The photo was captured at an angle, the arm and head or neck are involved, the patient is a female aged 30–39:
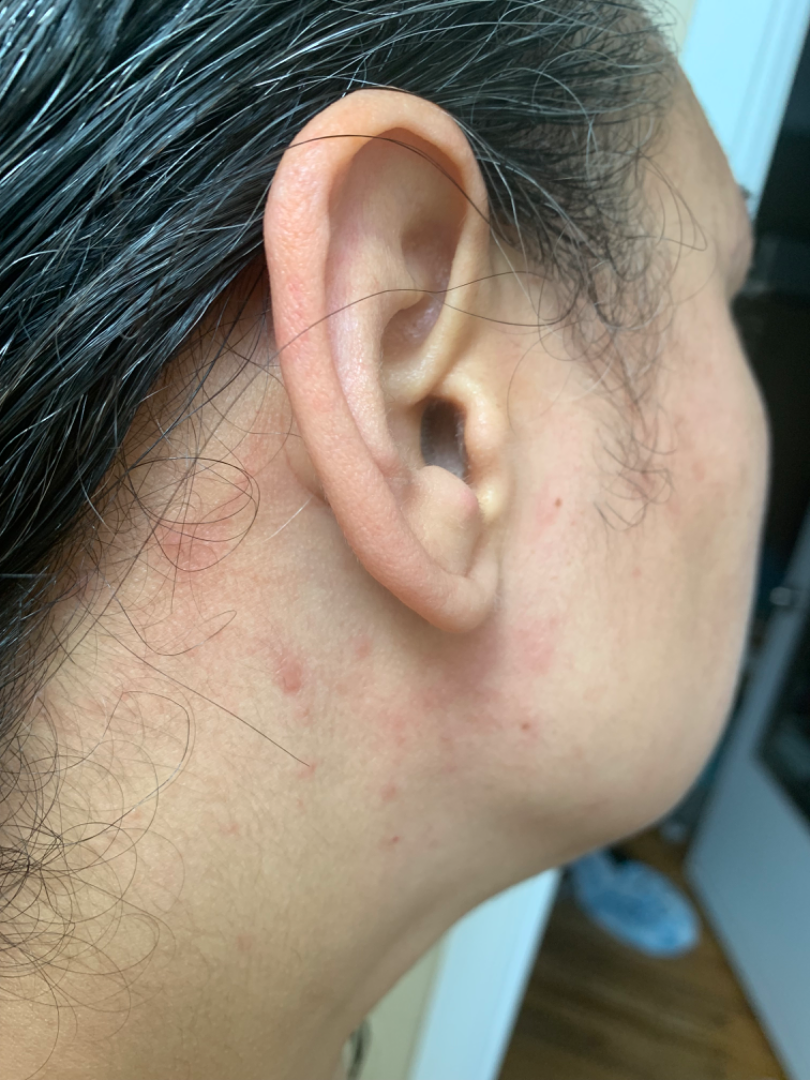On photographic review by a dermatologist: Allergic Contact Dermatitis (weight 0.54); Photodermatitis (weight 0.23); Folliculitis (weight 0.23).